This is a close-up image. The lesion involves the leg and arm — 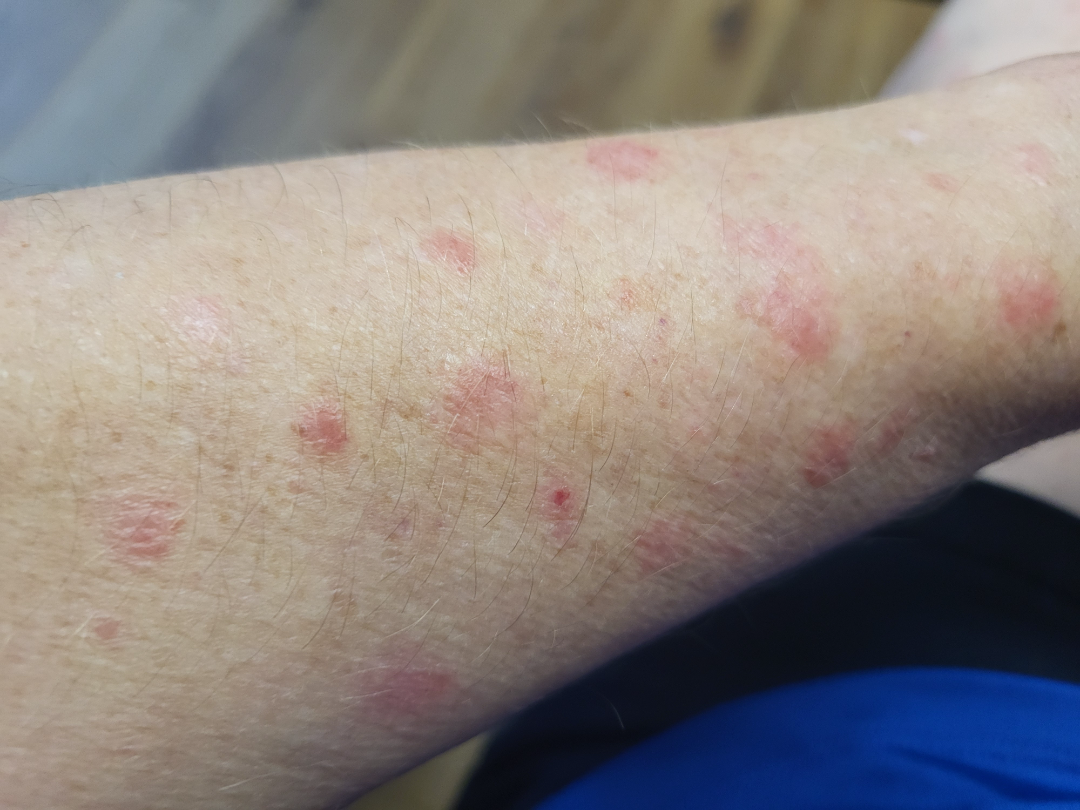Q: What was the assessment?
A: could not be assessed
Q: Any systemic symptoms?
A: none reported
Q: How does the lesion feel?
A: raised or bumpy and rough or flaky
Q: What symptoms does the patient report?
A: bothersome appearance
Q: How long has this been present?
A: one to four weeks